A skin lesion imaged with a dermatoscope:
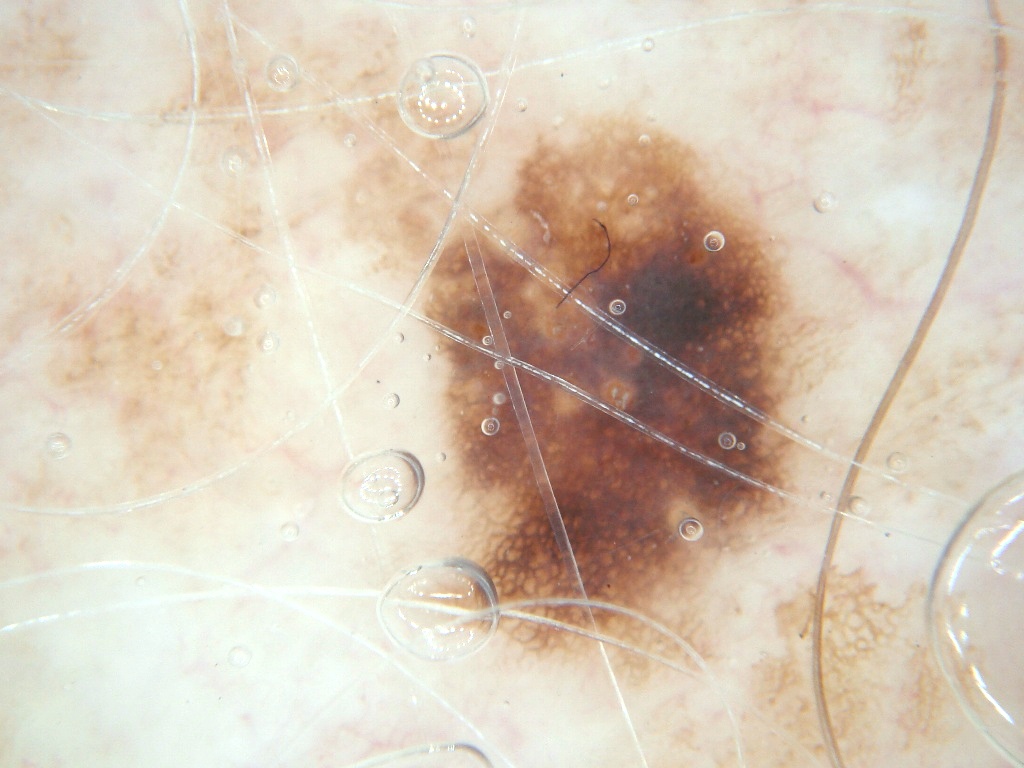absent dermoscopic findings = streaks and globules
bounding box = 379, 103, 819, 699
impression = a benign lesion